A dermoscopic image of a skin lesion.
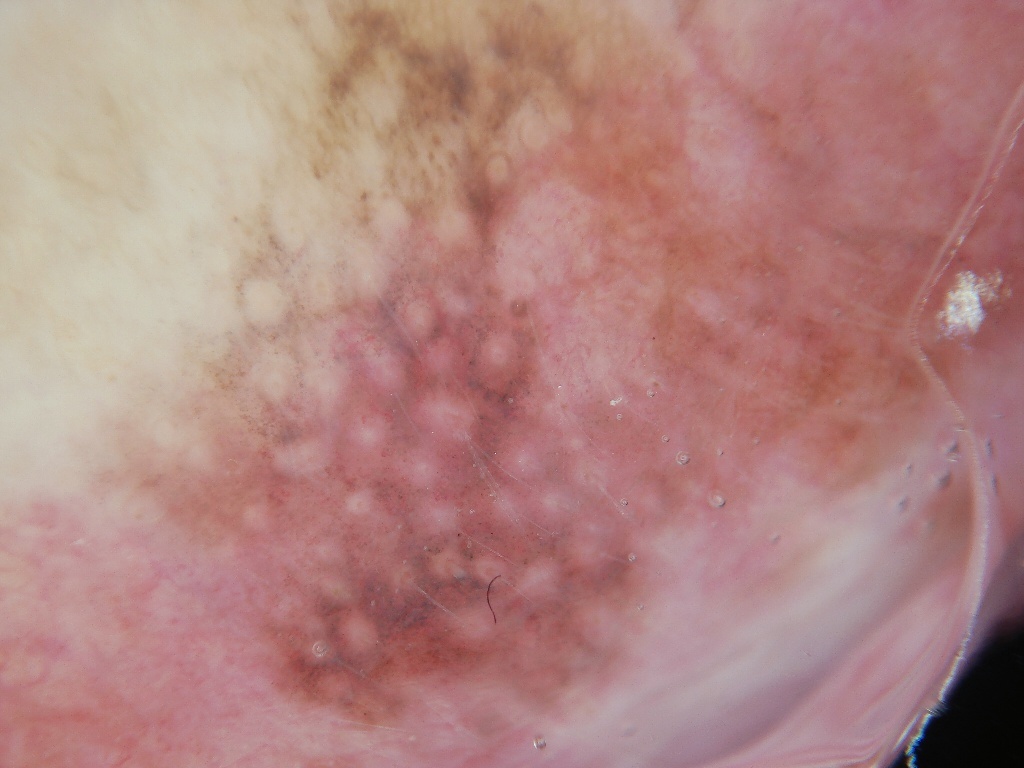Q: What is the lesion's bounding box?
A: reaches across the whole image
Q: What is this lesion?
A: a malignant lesion